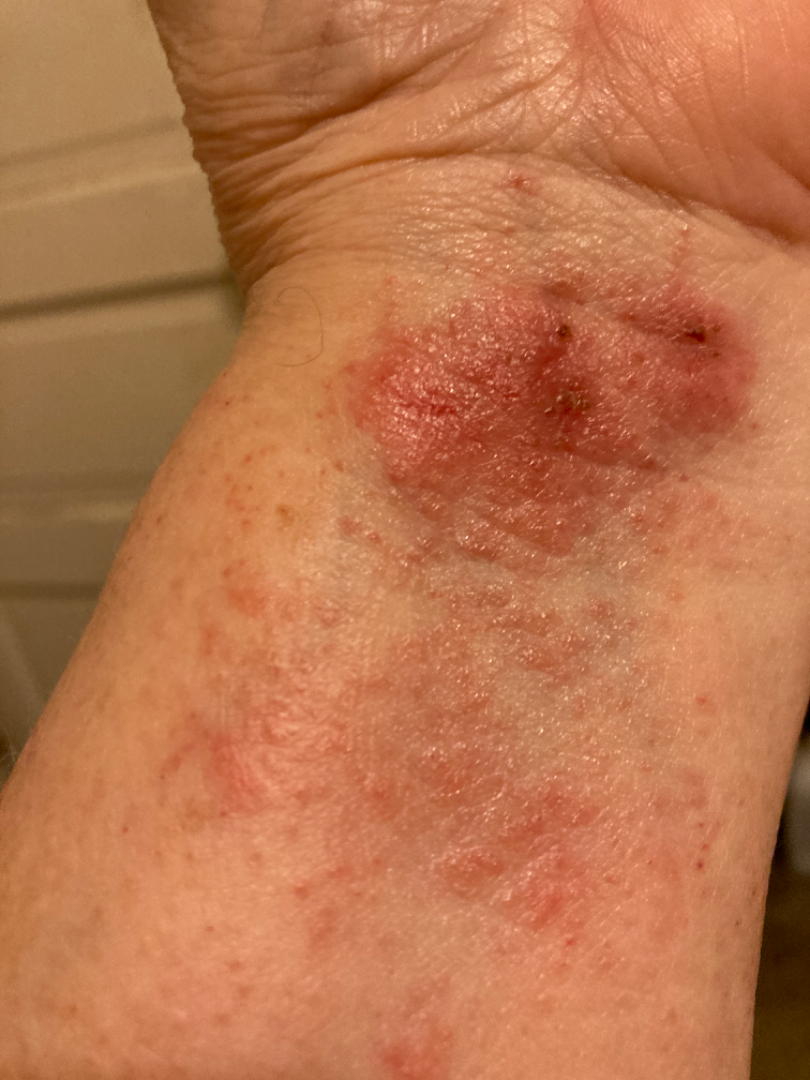The patient reports the lesion is raised or bumpy. The lesion involves the arm. Female contributor, age 70–79. The patient considered this a rash. FST II. The patient reports associated fatigue. Reported lesion symptoms include itching, burning and pain. Close-up view. On remote dermatologist review: Allergic Contact Dermatitis (most likely); Crusted eczematous dermatitis (considered); Eczema (considered); Secondary impetiginization (lower probability).